Female contributor, age 18–29; skin tone: Fitzpatrick skin type I; the patient considered this a rash; the head or neck and front of the torso are involved; the photo was captured at an angle; present for less than one week; reported lesion symptoms include itching — 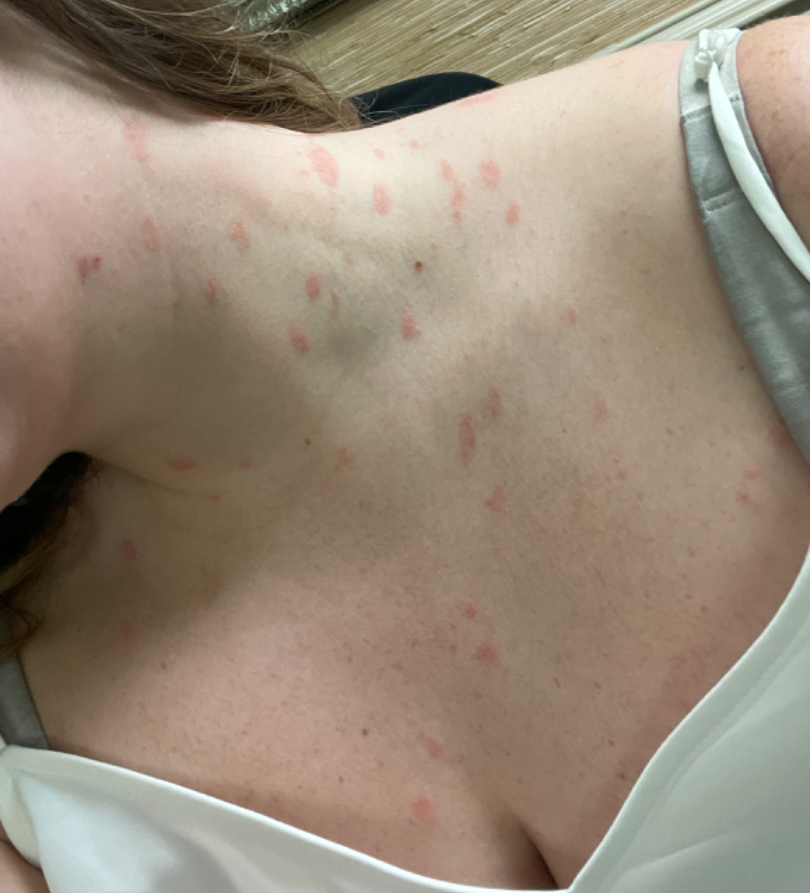Most consistent with Pityriasis rosea; also raised was Psoriasis.